A dermoscopic photograph of a skin lesion.
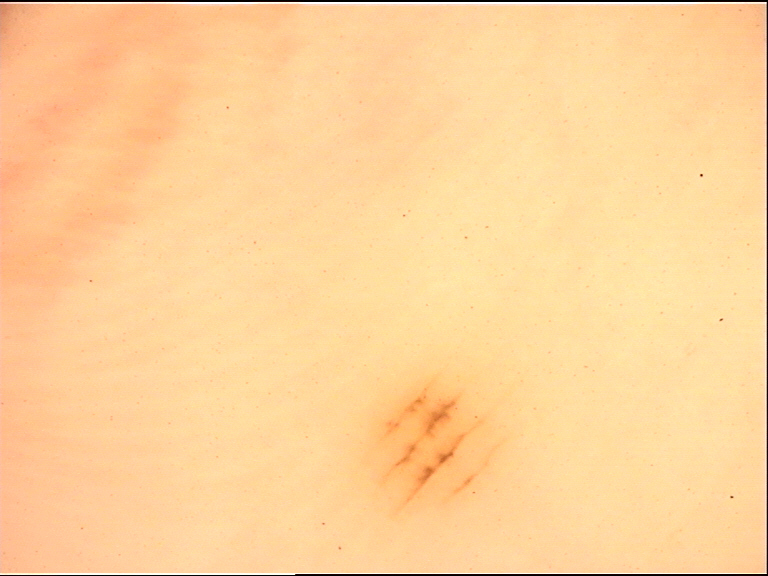Case:
* diagnosis: acral junctional nevus (expert consensus)